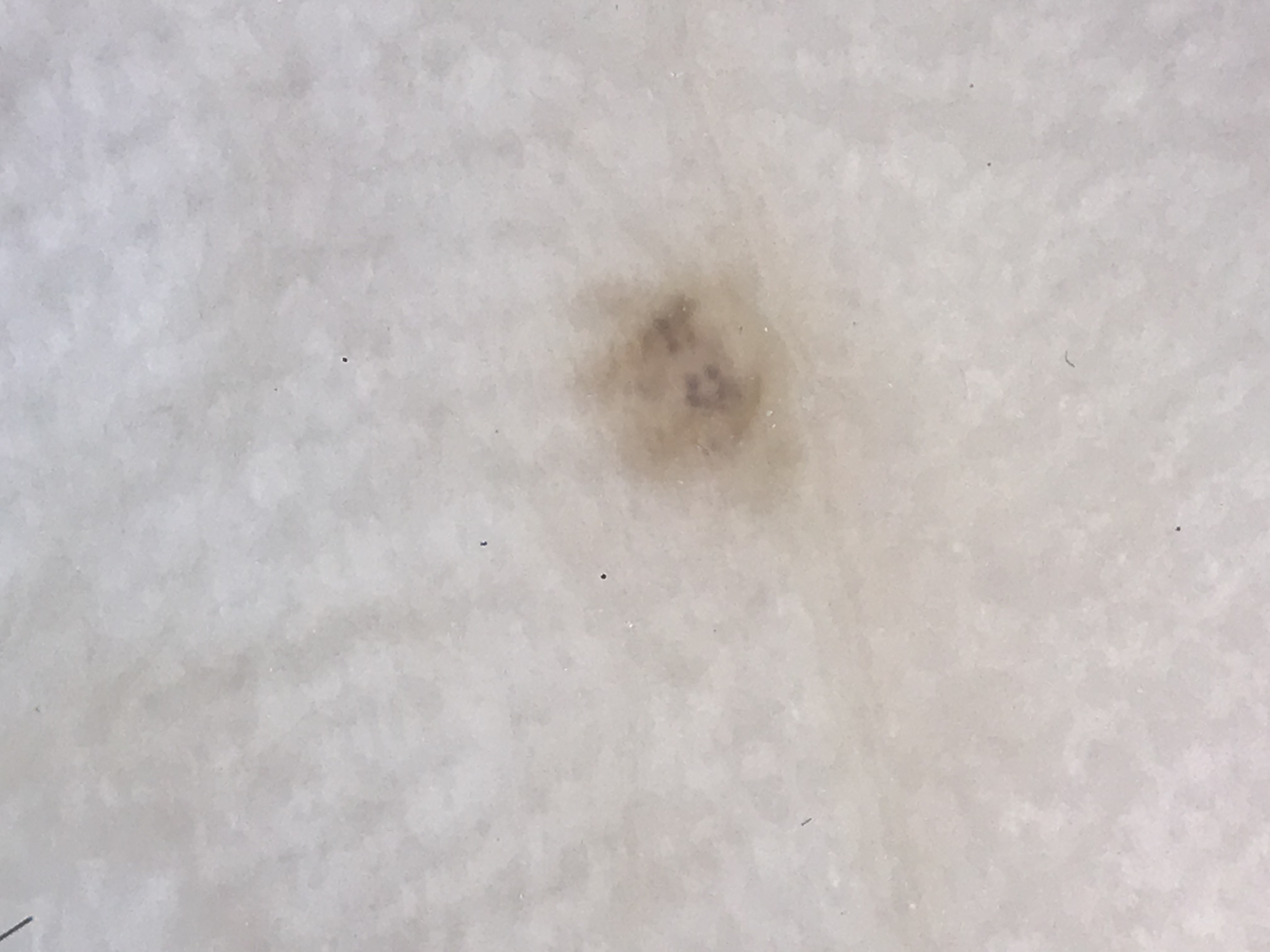A dermoscopic image of a skin lesion.
The architecture is that of a banal lesion.
Diagnosed as an acral junctional nevus.